A male subject, in their mid- to late 50s · a dermatoscopic image of a skin lesion: 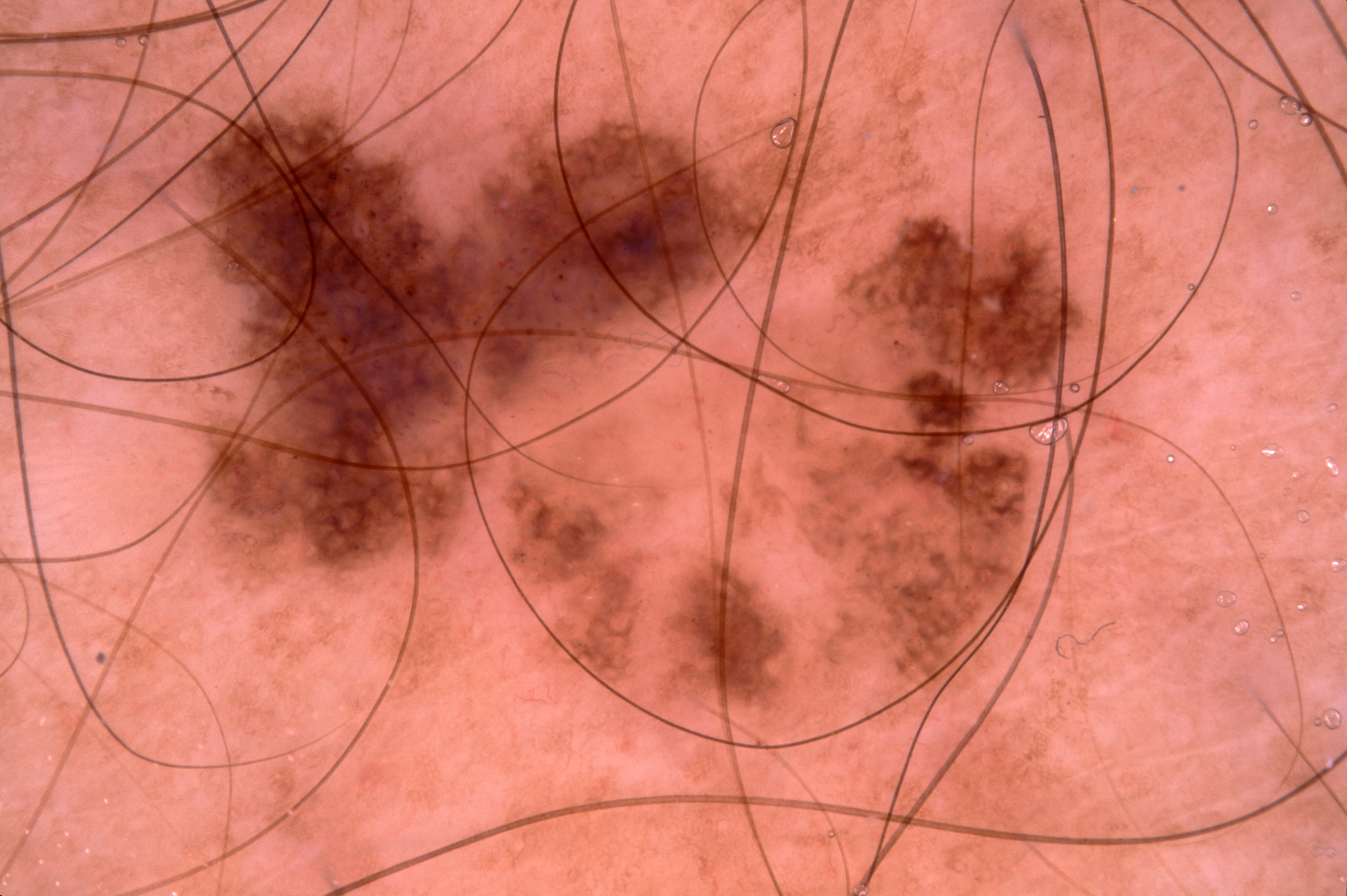Q: Where is the lesion located?
A: box(190, 105, 1137, 707)
Q: Lesion extent?
A: large
Q: What dermoscopic features are present?
A: pigment network and milia-like cysts; absent: streaks and negative network
Q: What is this lesion?
A: a seborrheic keratosis